Collected as part of a research study, without a referral diagnosis · a clinical photograph showing a skin lesion · the patient describes having a moderate number of moles — 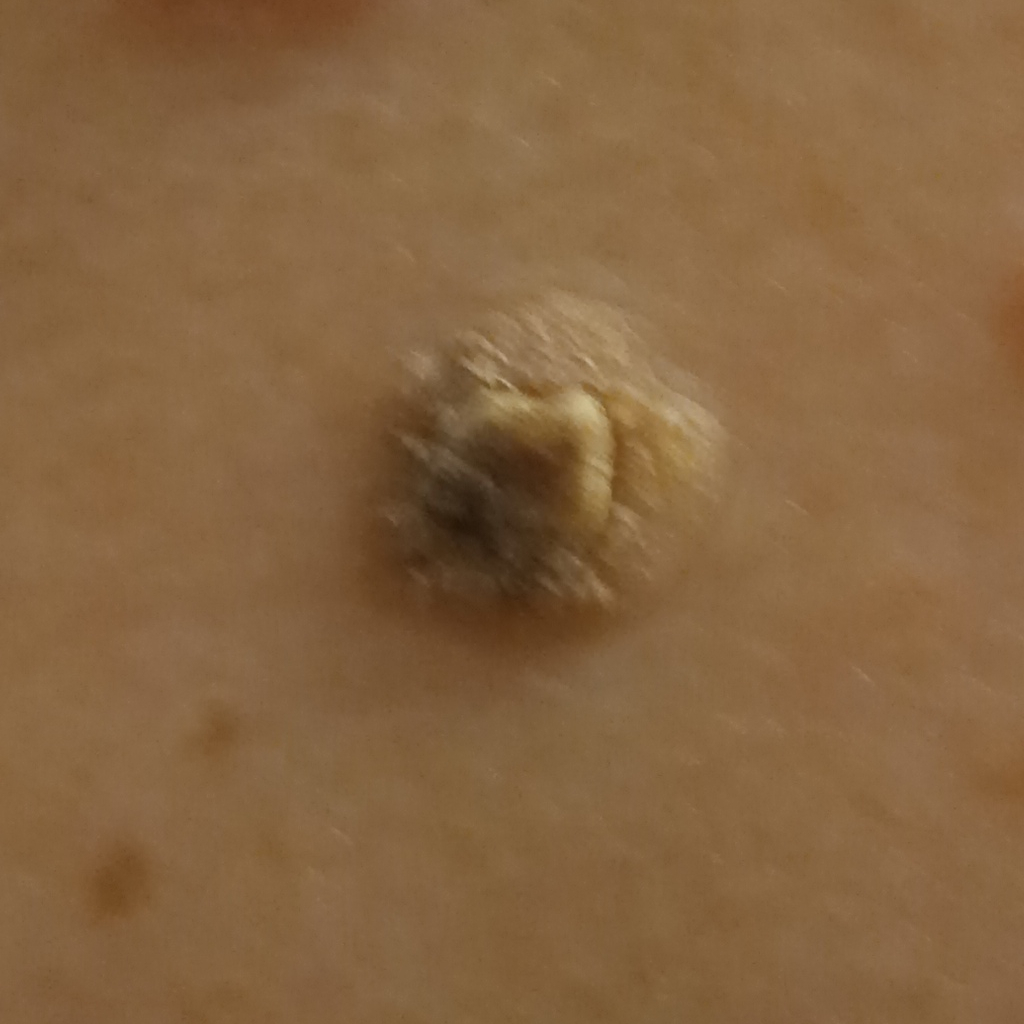Findings:
– diagnostic label · seborrheic keratosis (dermatologist consensus)